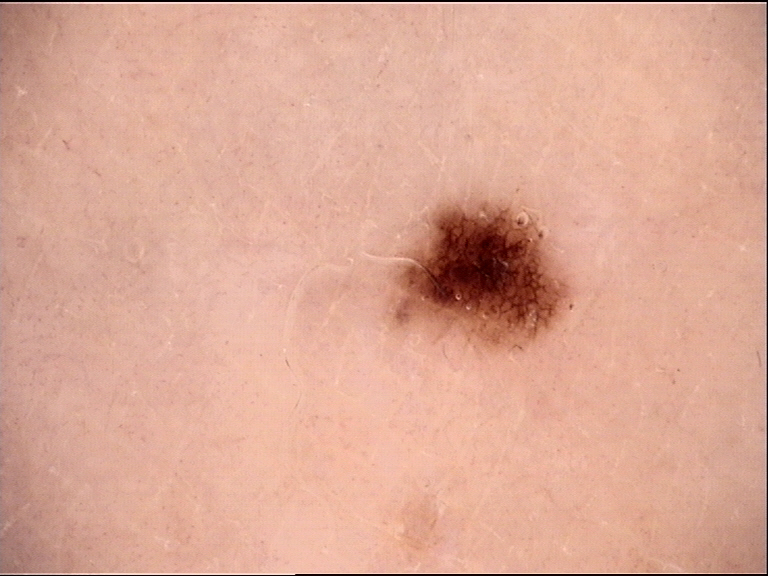Dermoscopy of a skin lesion.
Diagnosed as a dysplastic junctional nevus.